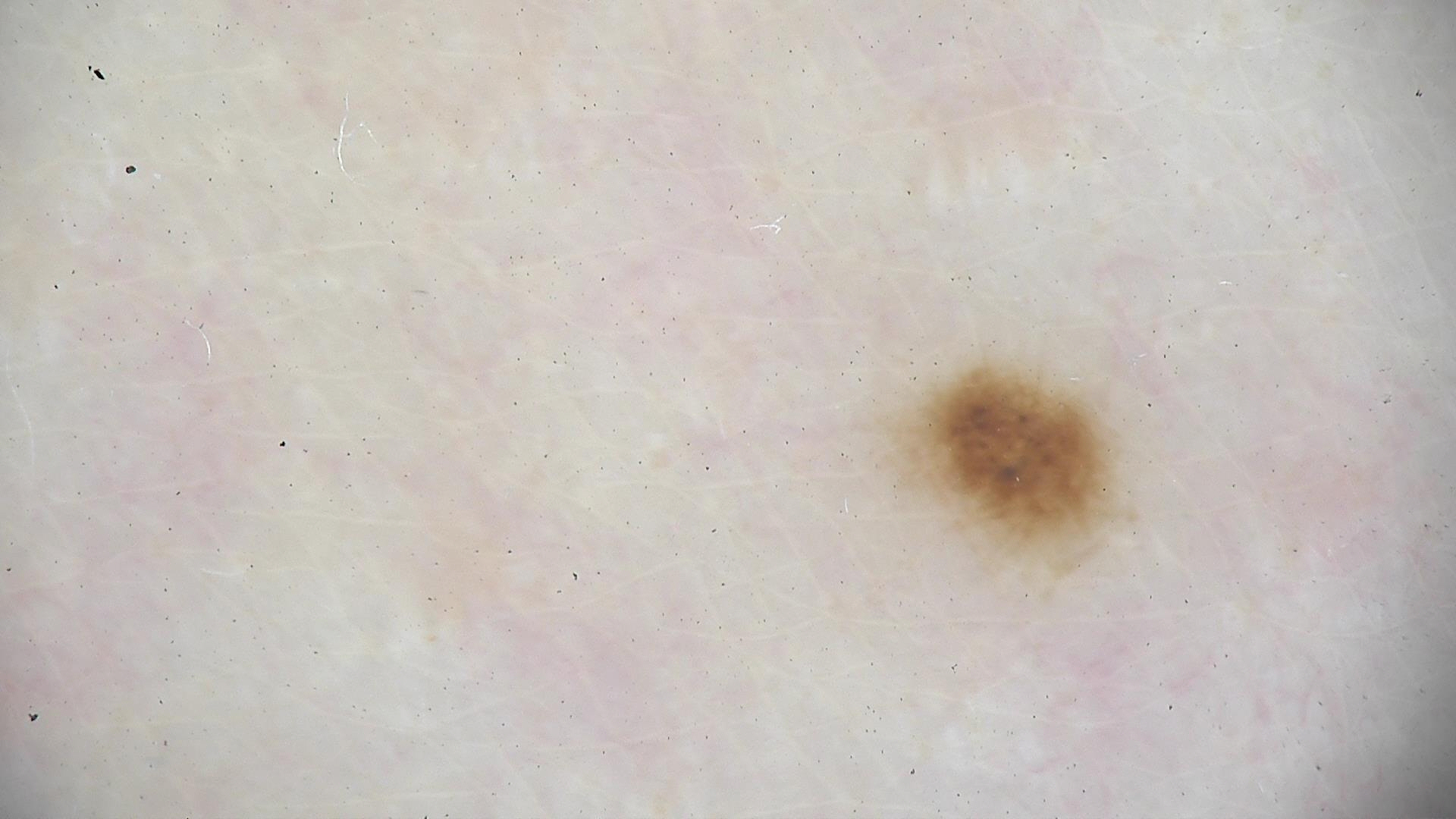Diagnosed as a dysplastic junctional nevus.